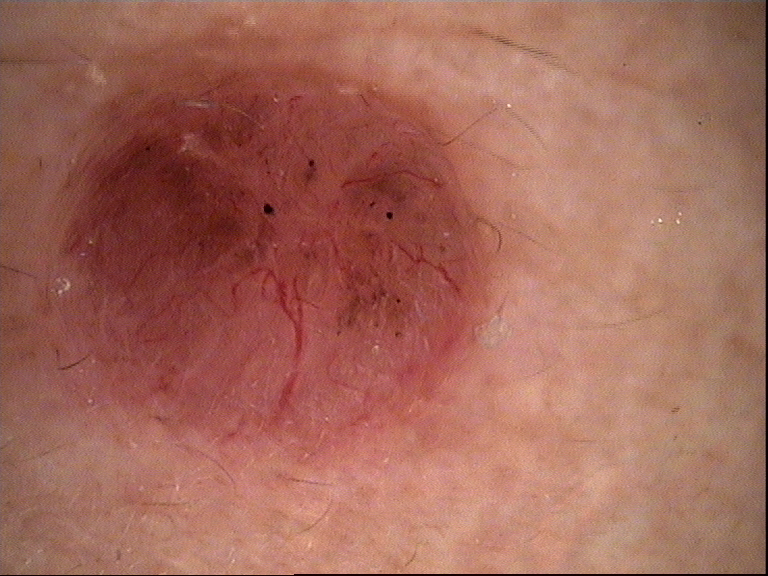Histopathologically confirmed as a basal cell carcinoma.